A dermoscopic photograph of a skin lesion:
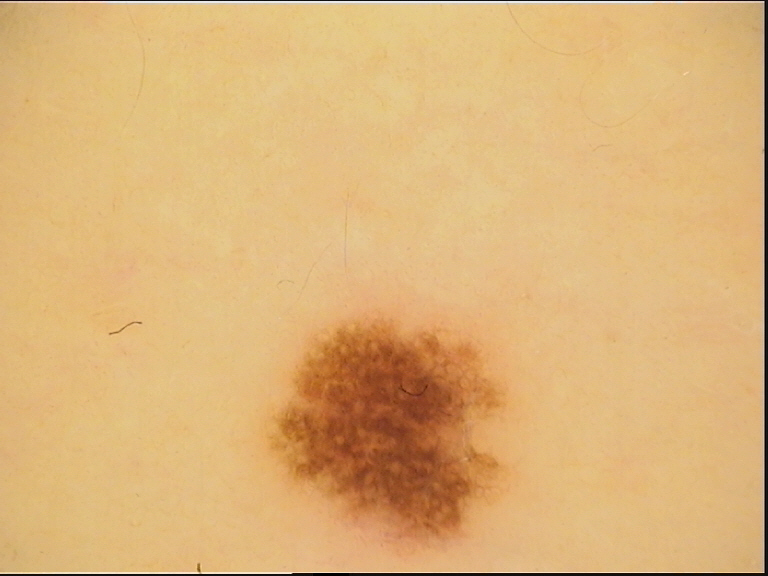diagnostic label: dysplastic junctional nevus (expert consensus).